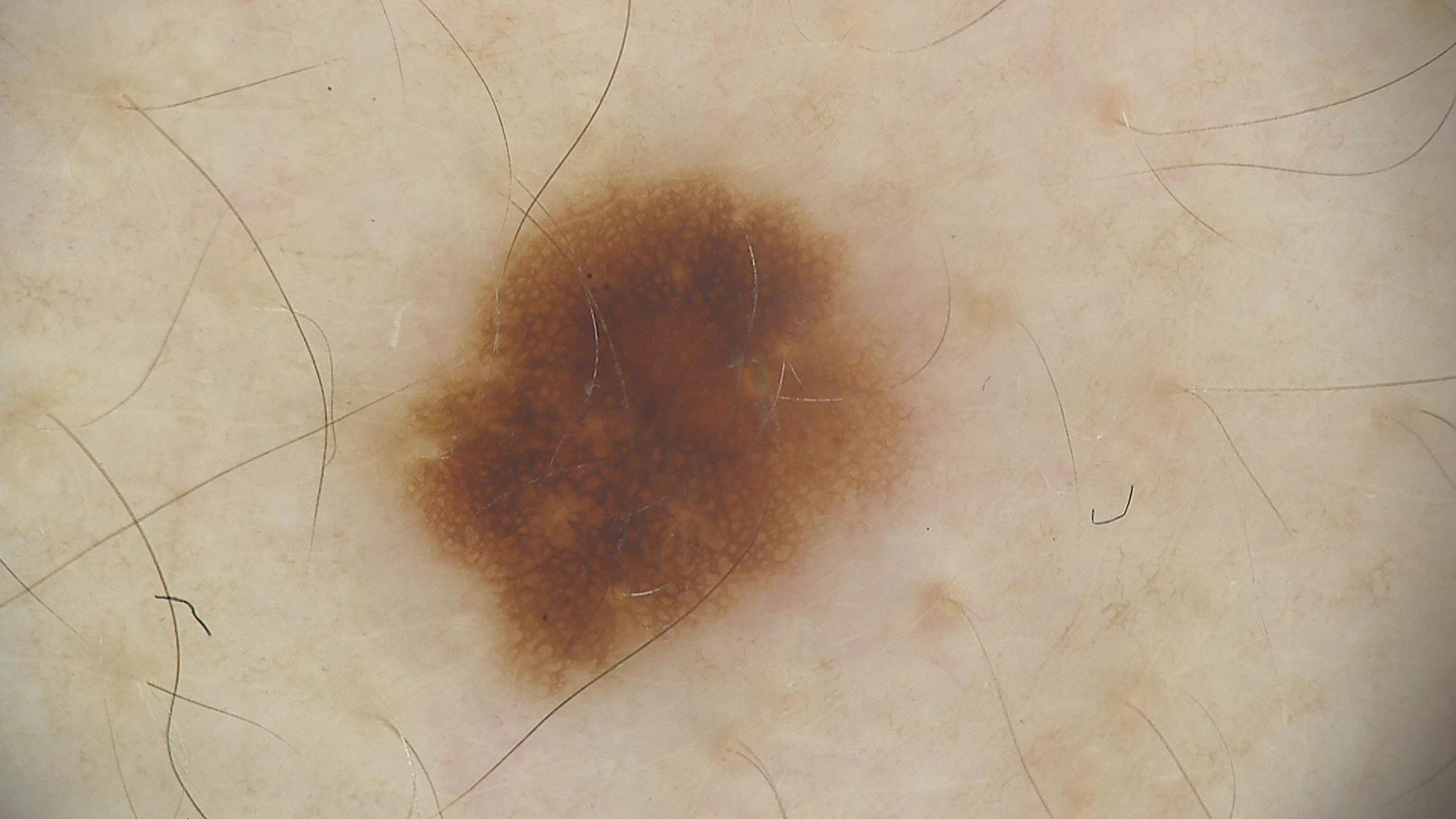diagnostic label: dysplastic junctional nevus (expert consensus)